A dermatoscopic image of a skin lesion:
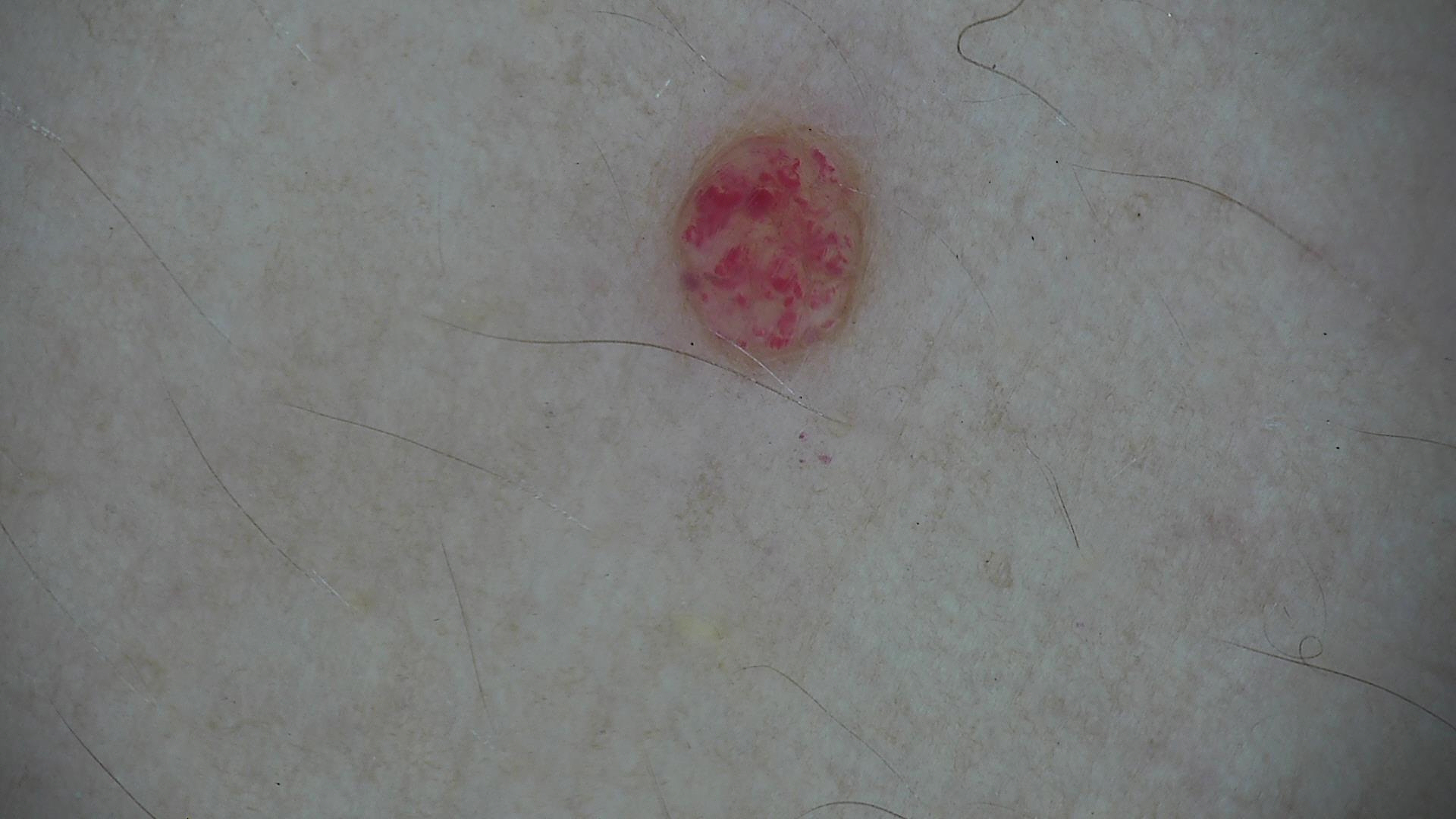class — hemangioma (expert consensus).